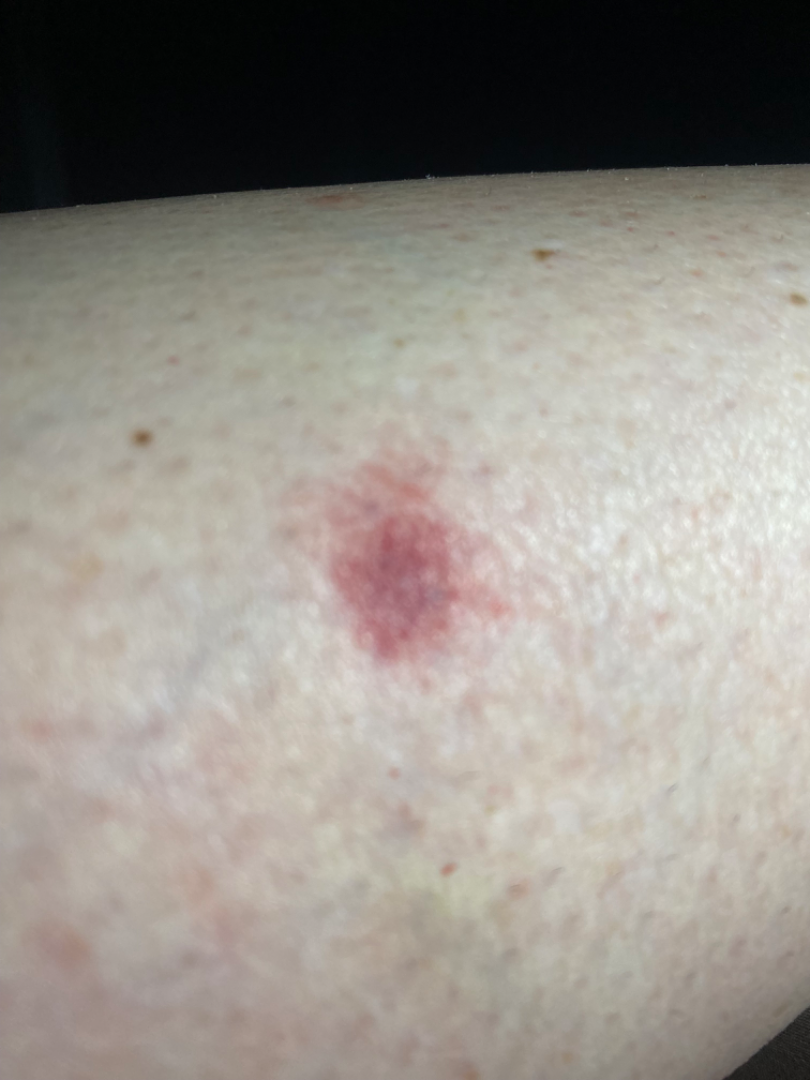The case was indeterminate on photographic review. The leg is involved. The patient described the issue as a rash. FST III. The subject is a female aged 50–59. Present for less than one week. The lesion is described as flat. The lesion is associated with itching and bothersome appearance. This is a close-up image.